Female patient, age 50–59. The patient notes burning and bothersome appearance. The patient also reports shortness of breath, fever and fatigue. The leg and top or side of the foot are involved. The patient considered this a rash. Texture is reported as raised or bumpy and fluid-filled. An image taken at a distance — 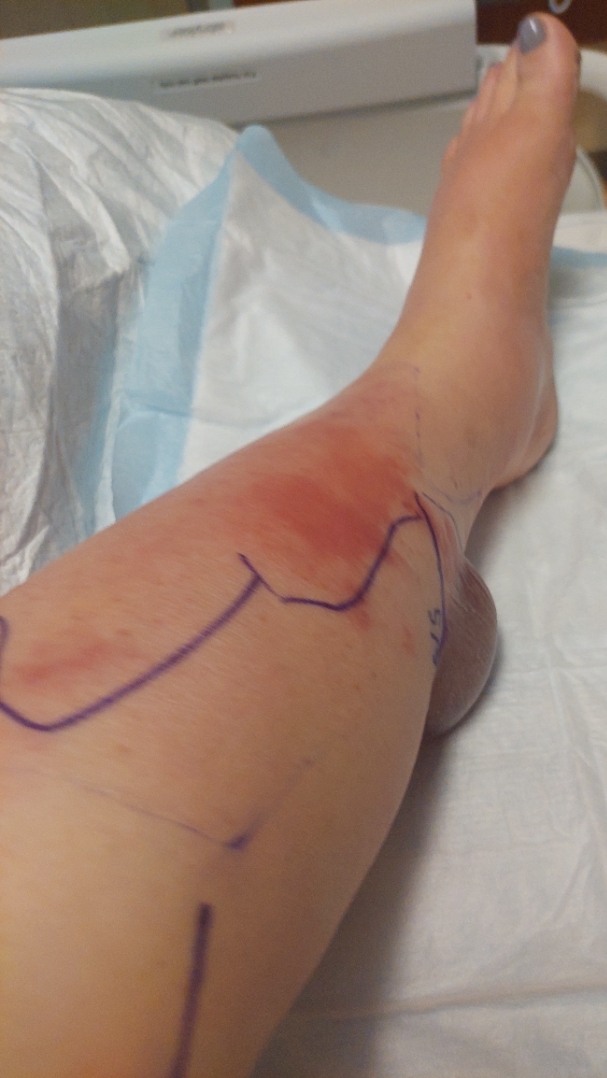<case>
<differential>Skin and soft tissue atypical mycobacterial infection, hemorrhagic bullae</differential>
</case>